The leg is involved. The patient is 50–59, female. A close-up photograph:
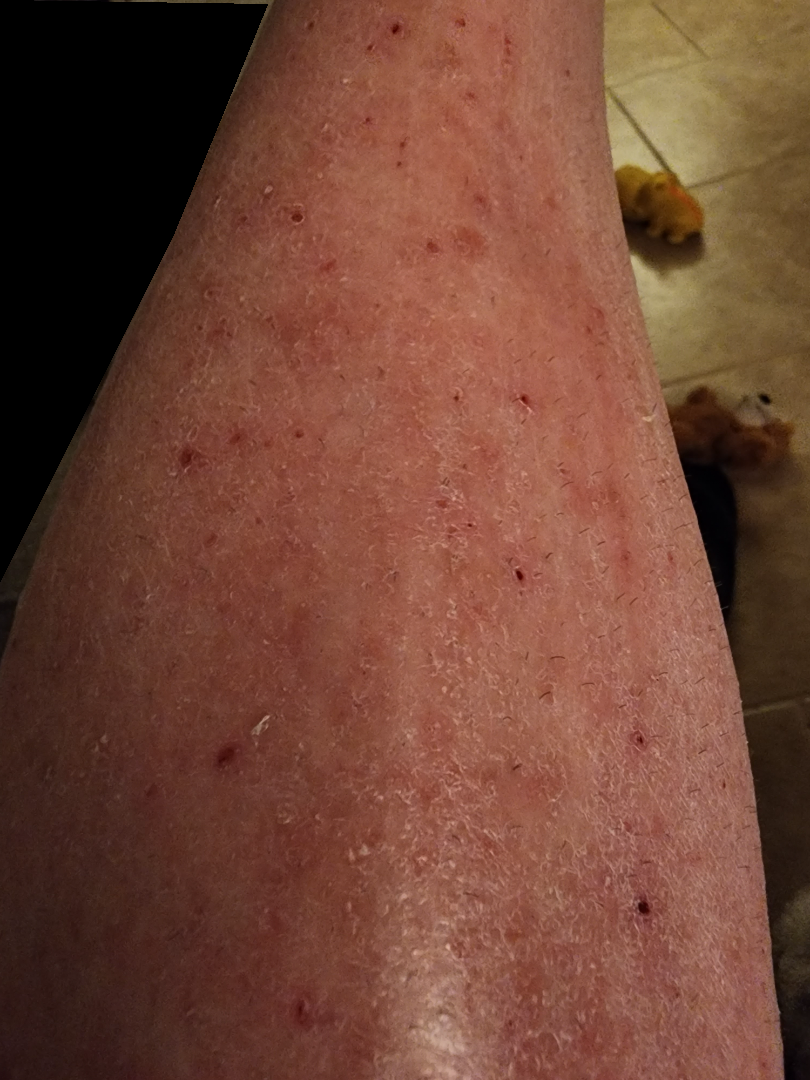Review: On remote review of the image: the primary impression is Eczema; an alternative is Xerosis; less likely is Stasis Dermatitis.